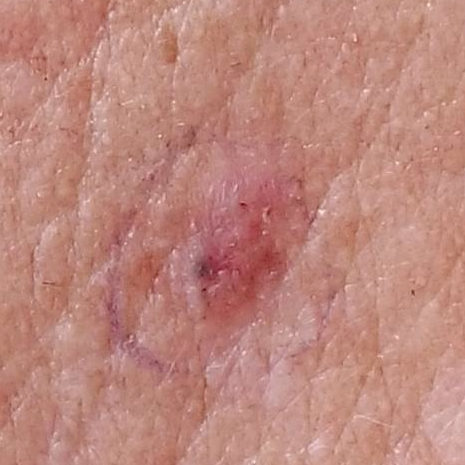A clinical close-up photograph of a skin lesion.
A female patient in their early 60s.
Located on the chest.
The patient reports that the lesion is elevated and itches.
Histopathological examination showed a basal cell carcinoma.